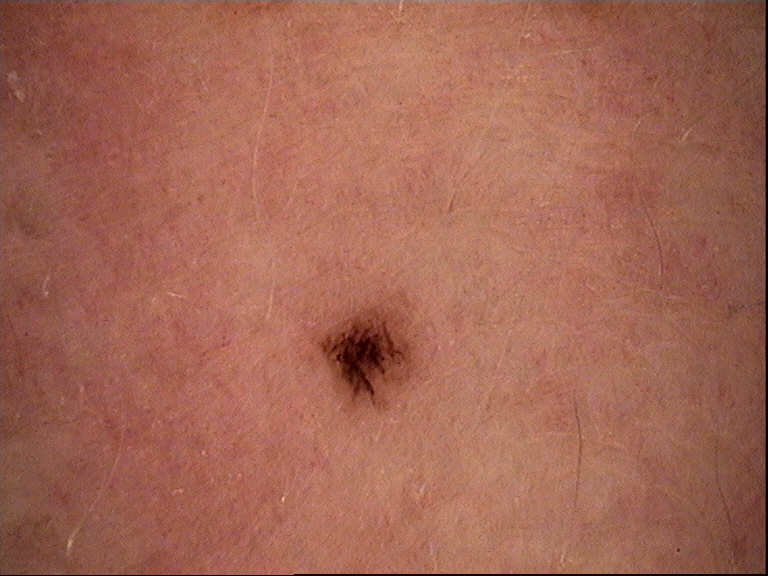diagnosis:
  name: dysplastic junctional nevus
  code: jd
  malignancy: benign
  super_class: melanocytic
  confirmation: expert consensus